Female patient, age 40–49; this image was taken at a distance; the lesion is described as raised or bumpy — 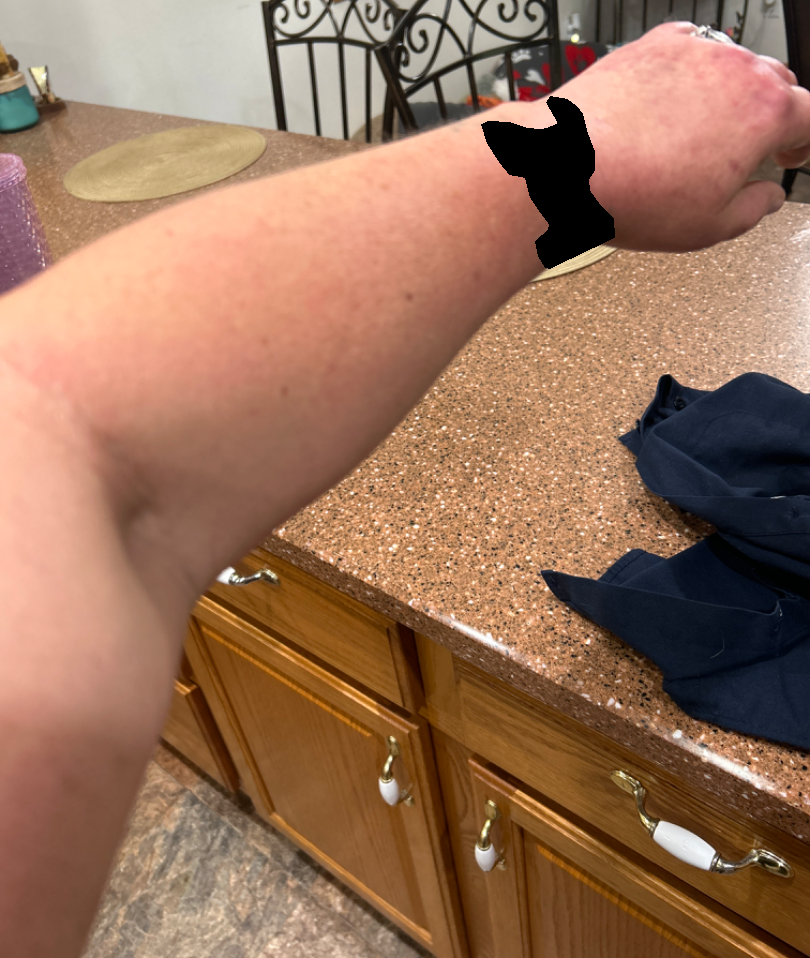Findings: Most consistent with Eczema.